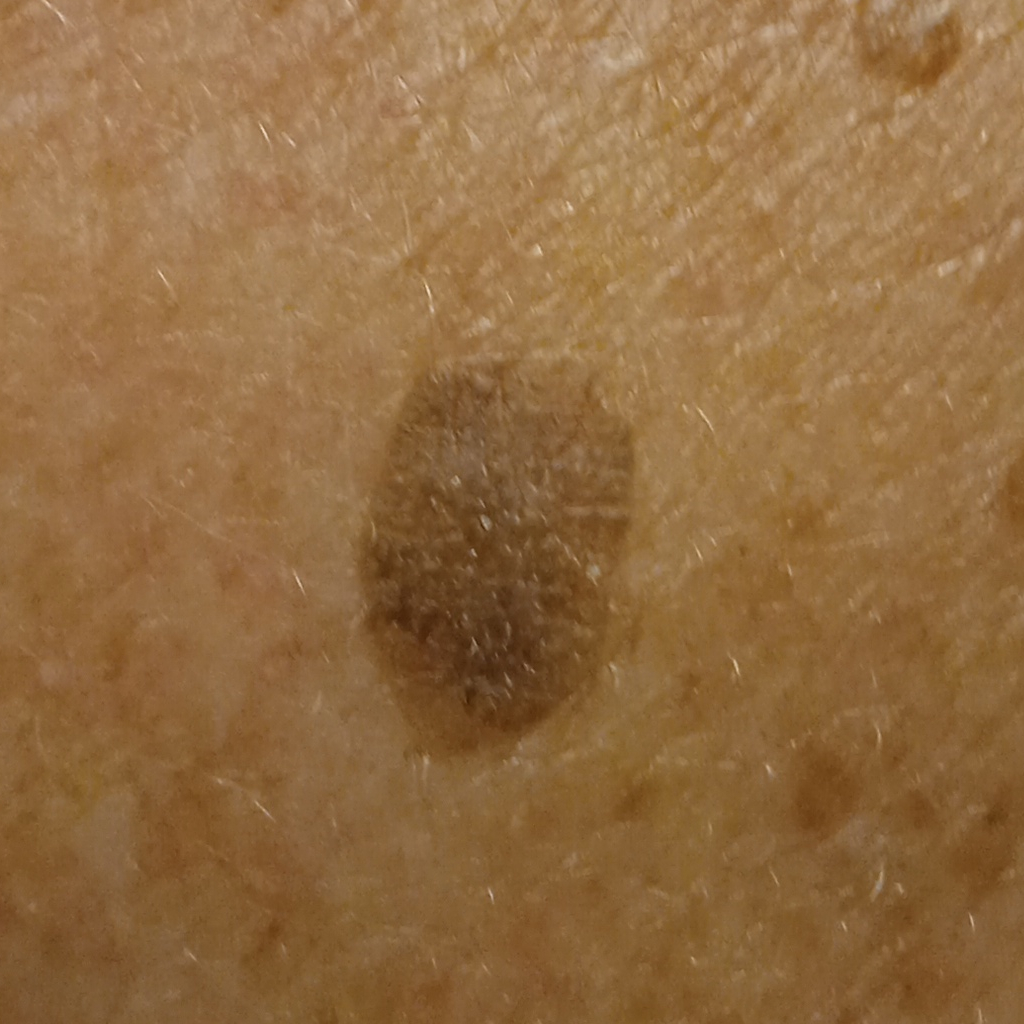On a questionnaire the patient reported no prior organ transplant.
A clinical photograph showing a skin lesion.
Imaged for a research study, with no referral diagnosis recorded.
A female subject age 78.
The patient says their skin tans without first burning.
Numerous moles by the patient's own estimate.
Located on the back.
The lesion is about 9.6 mm across.
The diagnostic impression was a seborrheic keratosis.